A male subject, aged around 40 · a dermoscopy image of a single skin lesion — 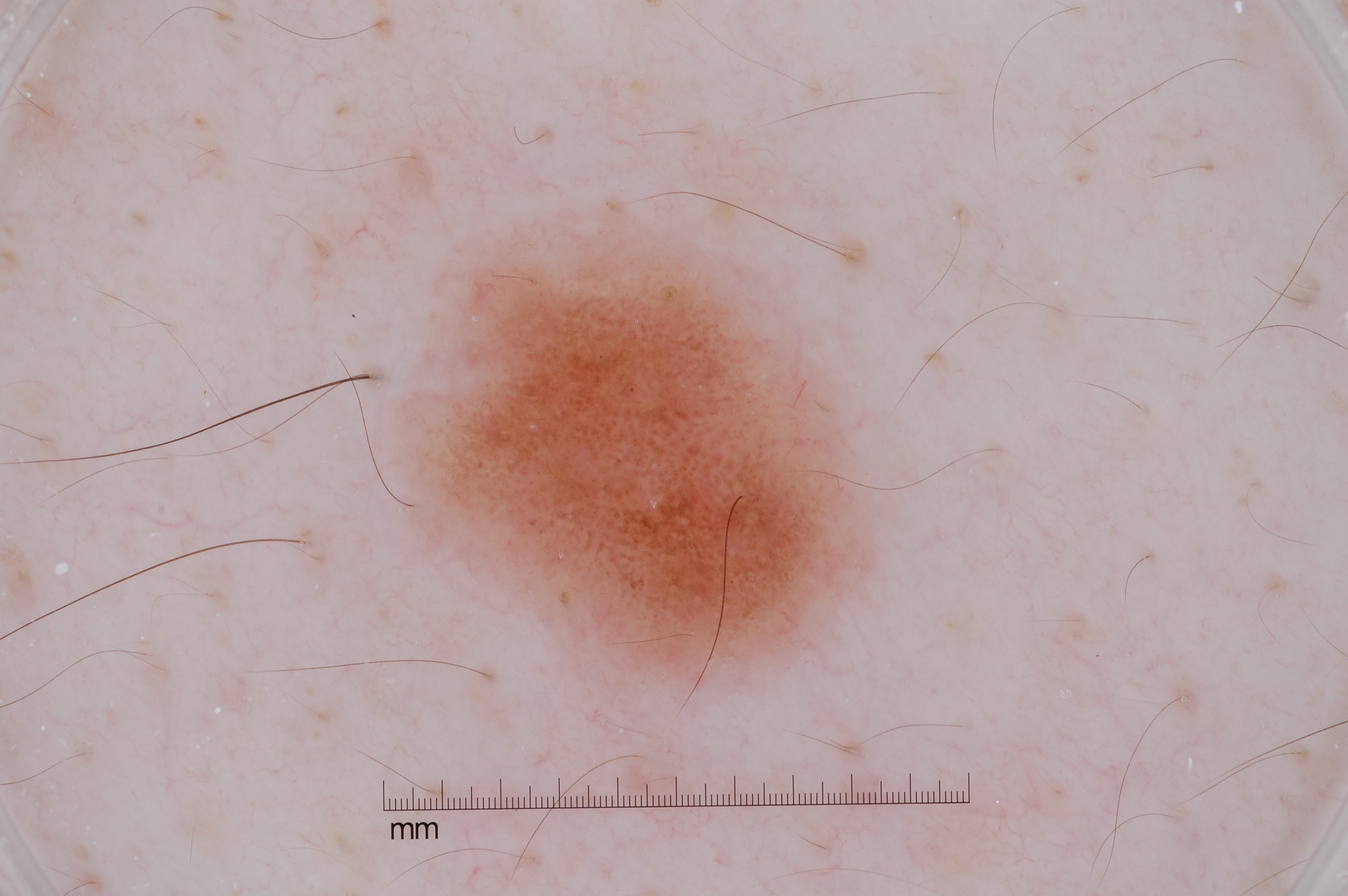{
  "dermoscopic_features": {
    "present": [
      "negative network",
      "milia-like cysts"
    ],
    "absent": [
      "pigment network",
      "streaks"
    ]
  },
  "lesion_location": {
    "bbox_xyxy": [
      422,
      231,
      863,
      686
    ]
  },
  "lesion_extent": "moderate",
  "diagnosis": {
    "name": "melanocytic nevus",
    "malignancy": "benign",
    "lineage": "melanocytic",
    "provenance": "clinical"
  }
}